A dermatoscopic image of a skin lesion:
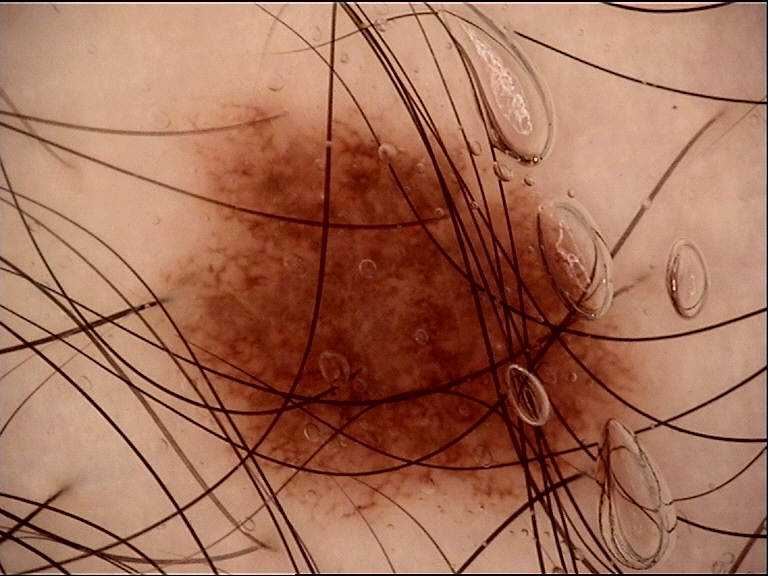The diagnostic label was a benign lesion — a dysplastic junctional nevus.